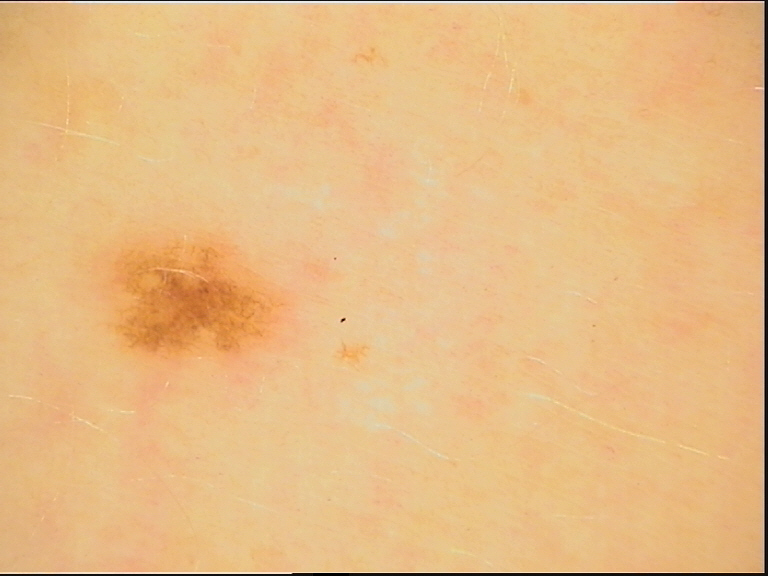Conclusion: Diagnosed as a benign lesion — a dysplastic junctional nevus.